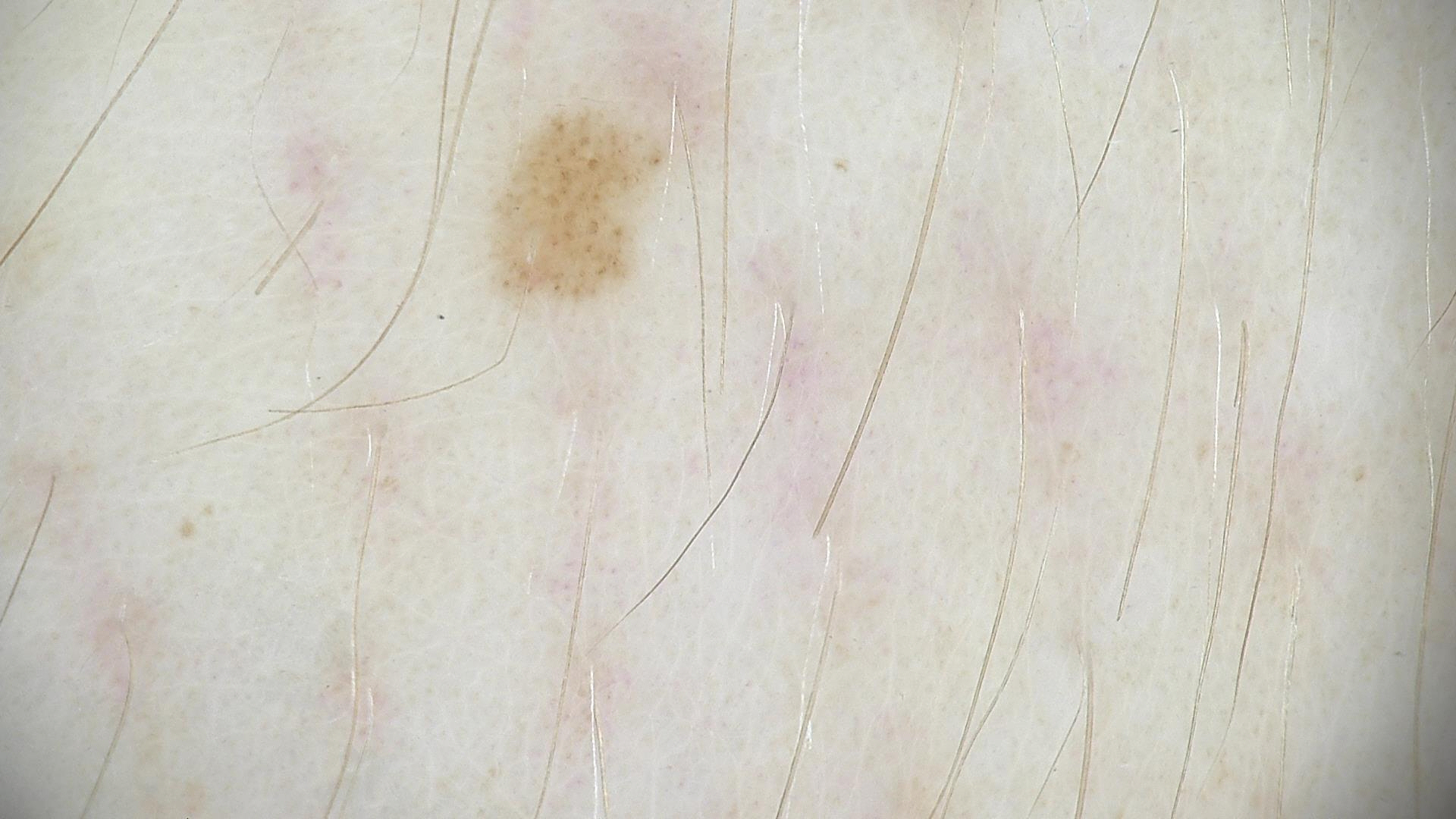A dermoscopic close-up of a skin lesion.
Consistent with a benign lesion — a dysplastic junctional nevus.